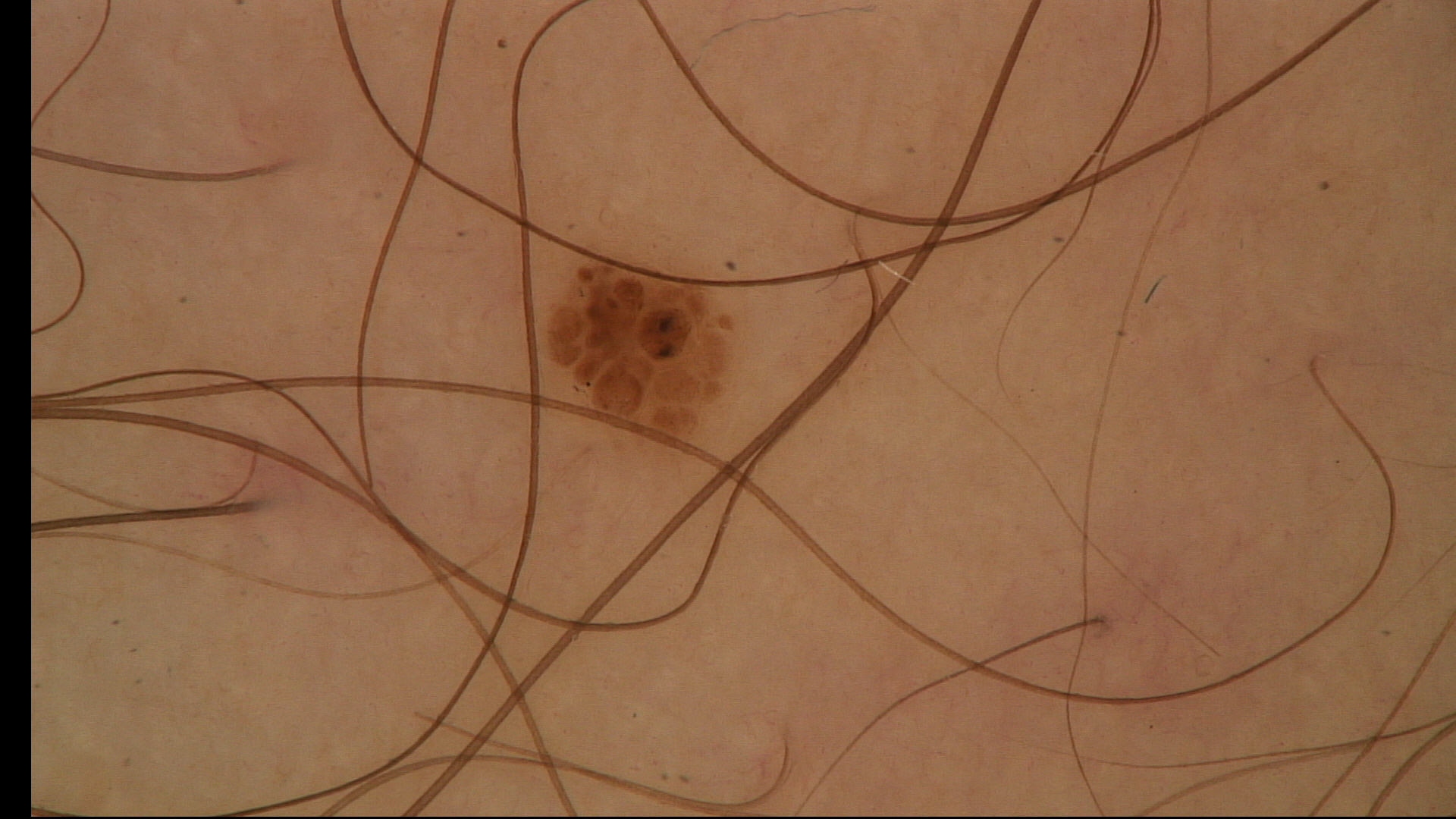A dermoscopic image of a skin lesion. This is a banal lesion. Consistent with a dermal nevus.